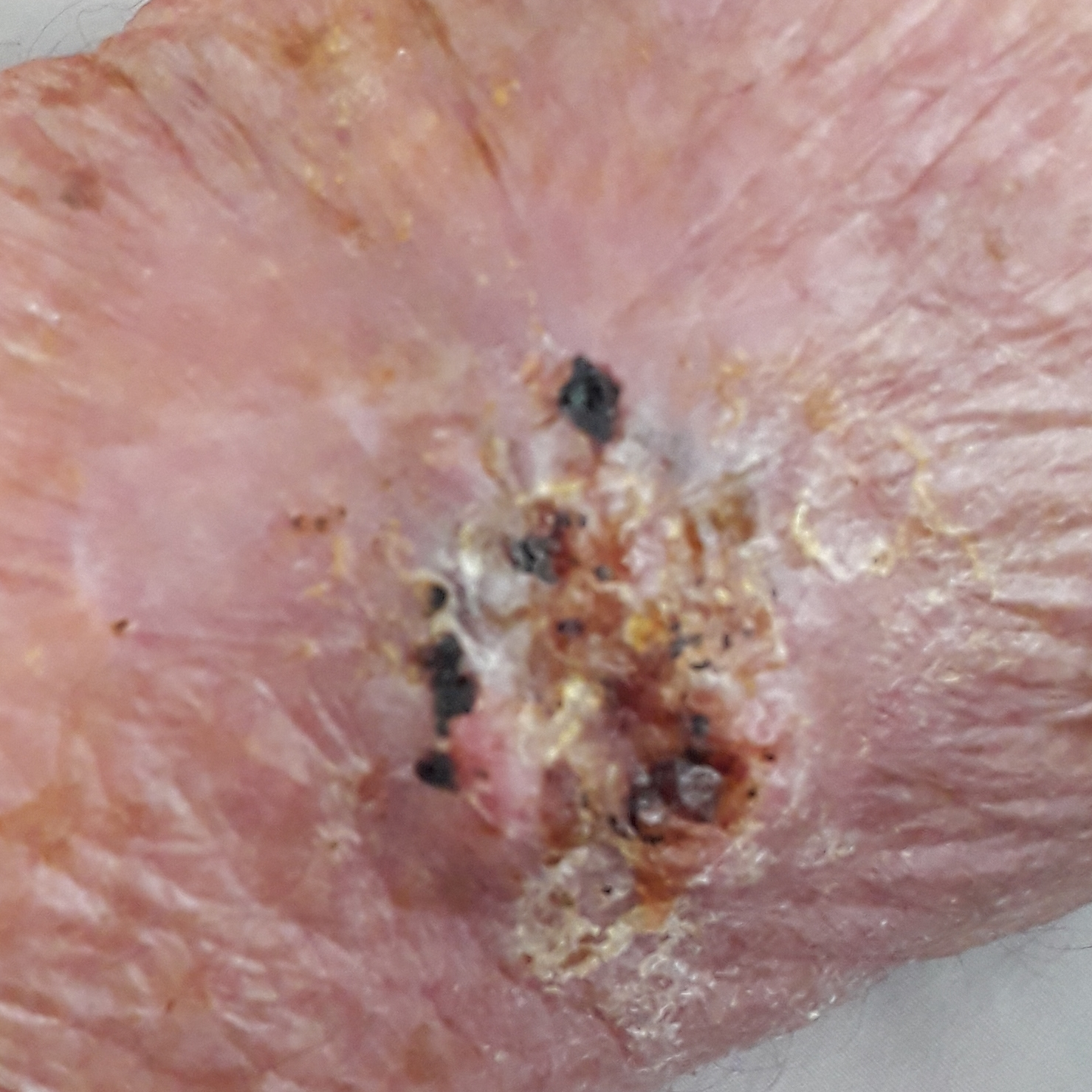By history, tobacco use and no alcohol use. The patient is Fitzpatrick phototype II. A male subject in their 80s. The lesion is located on a forearm. The lesion measures approximately 30 × 20 mm. By the patient's account, the lesion hurts, is elevated, has bled, and itches. Histopathologically confirmed as a basal cell carcinoma.